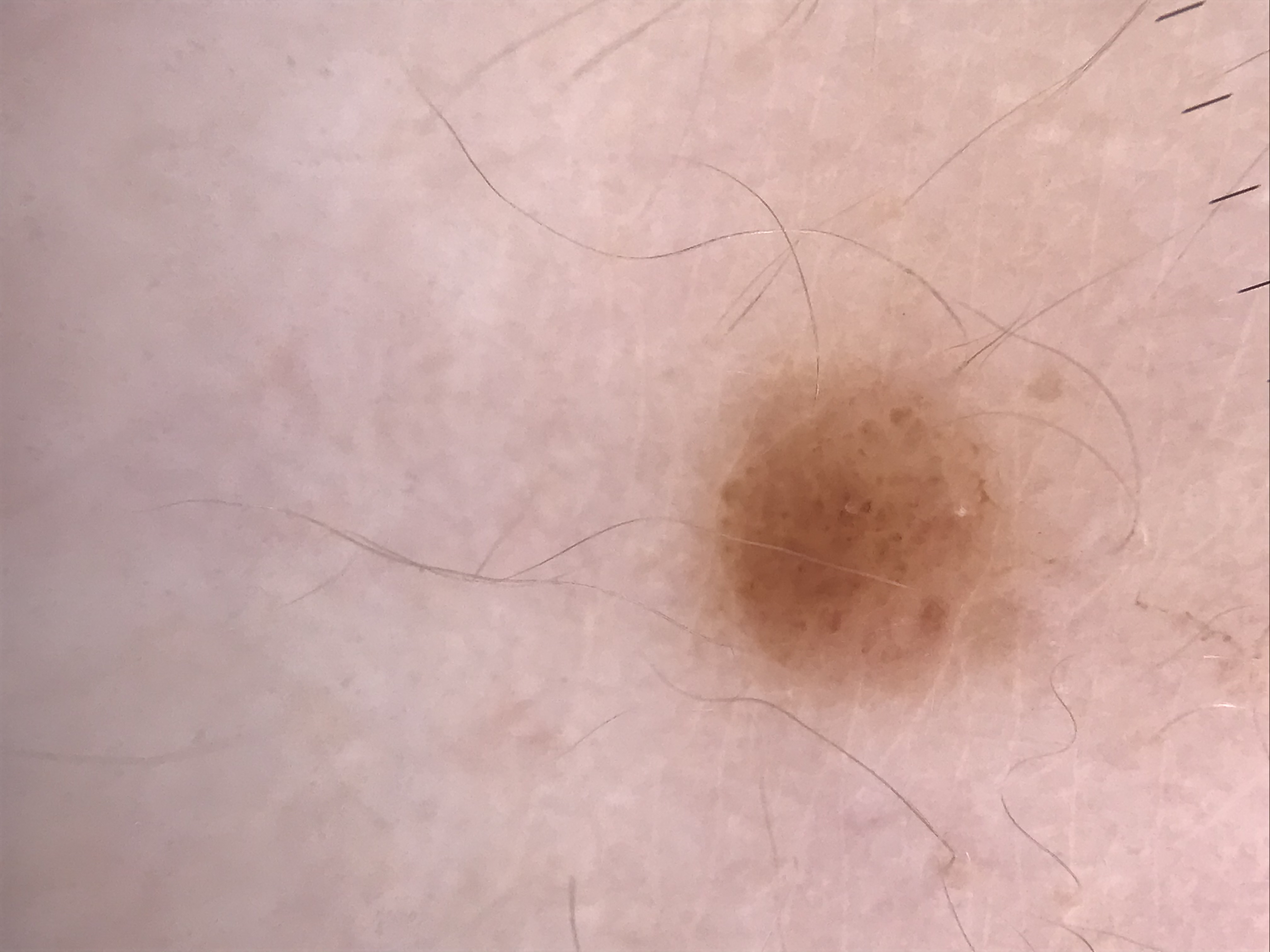image type: dermatoscopy
class: compound nevus (expert consensus)